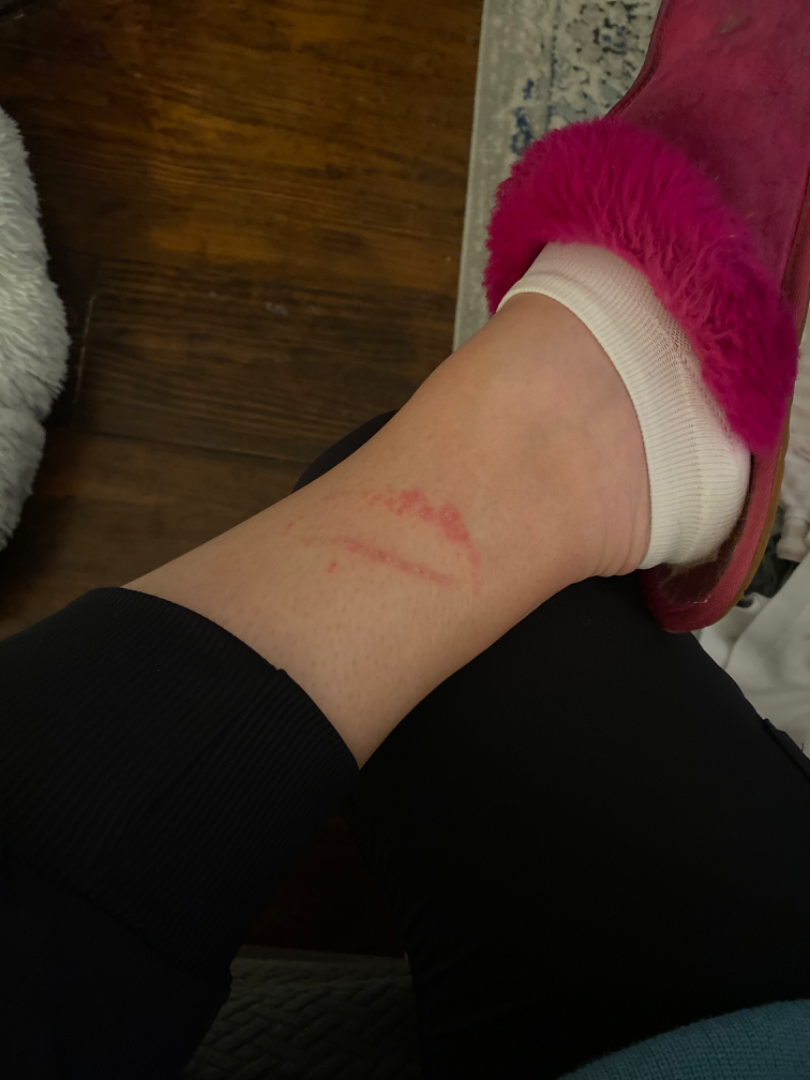- clinical impression — reviewed remotely by one dermatologist: in keeping with Allergic Contact Dermatitis